The arm is involved. The subject is 18–29, male. The photograph is a close-up of the affected area — 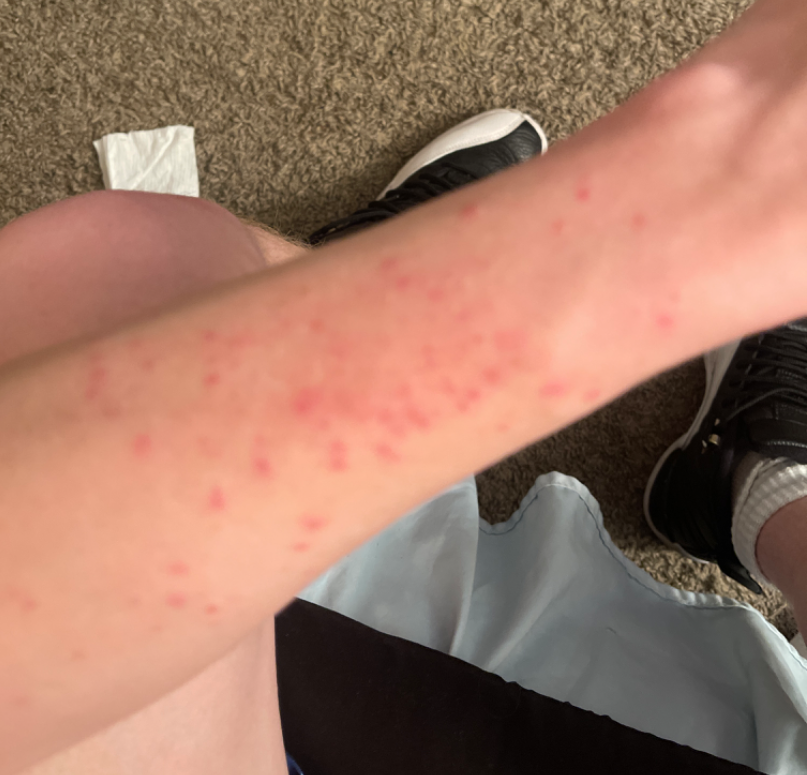Patient information: No relevant systemic symptoms. Symptoms reported: bothersome appearance. The patient notes the lesion is raised or bumpy and rough or flaky. Review: Insect Bite (favored); Eczema (possible); Scabies (possible).